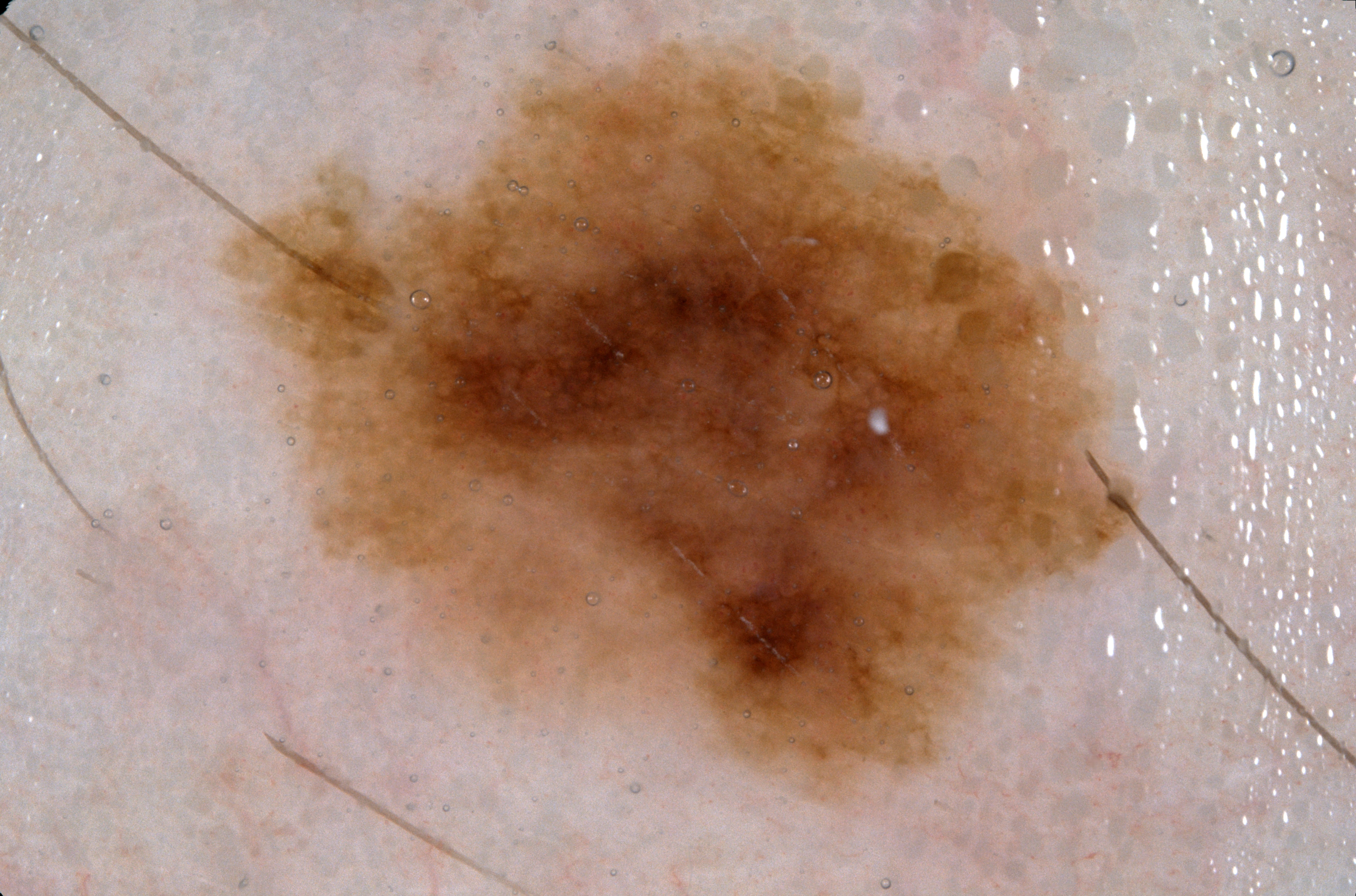Findings:
A female patient, roughly 55 years of age. A dermoscopic close-up of a skin lesion. A large lesion occupying much of the field. Dermoscopic assessment notes pigment network, with no milia-like cysts, streaks, or negative network. With coordinates (x1, y1, x2, y2), the lesion's extent is bbox(226, 42, 1181, 802).
Impression:
Diagnosed as a melanocytic nevus.